A male subject 62 years old. The chart notes alcohol use, prior malignancy (patient or family), prior skin cancer (patient or family), no pesticide exposure, and no tobacco use: 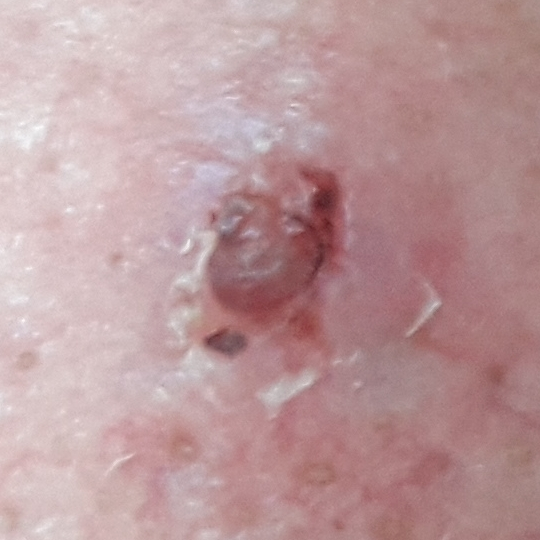<record>
  <lesion_location>the nose</lesion_location>
  <lesion_size>
    <diameter_1_mm>5.0</diameter_1_mm>
    <diameter_2_mm>4.0</diameter_2_mm>
  </lesion_size>
  <diagnosis>
    <name>basal cell carcinoma</name>
    <code>BCC</code>
    <malignancy>malignant</malignancy>
    <confirmation>histopathology</confirmation>
  </diagnosis>
</record>